Reported duration is about one day · an image taken at an angle · male patient, age 18–29 · the lesion is described as raised or bumpy and rough or flaky · the patient considered this a rash · the affected area is the palm and back of the hand · the lesion is associated with itching, enlargement, pain and burning · no constitutional symptoms were reported · skin tone: FST II; human graders estimated a Monk skin tone scale of 3:
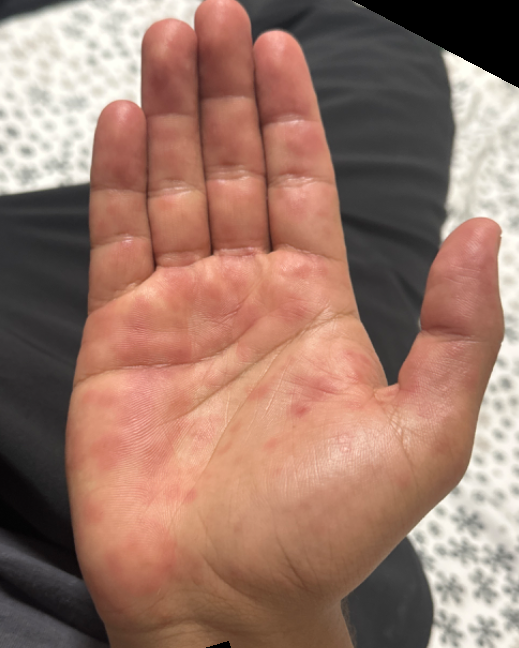Assessment: On teledermatology review: most consistent with Eczema; a more distant consideration is Allergic Contact Dermatitis; less likely is Viral Exanthem.